Symptoms reported: darkening; no associated systemic symptoms reported; the patient notes the condition has been present for three to twelve months; texture is reported as flat; an image taken at a distance; the lesion involves the back of the hand:
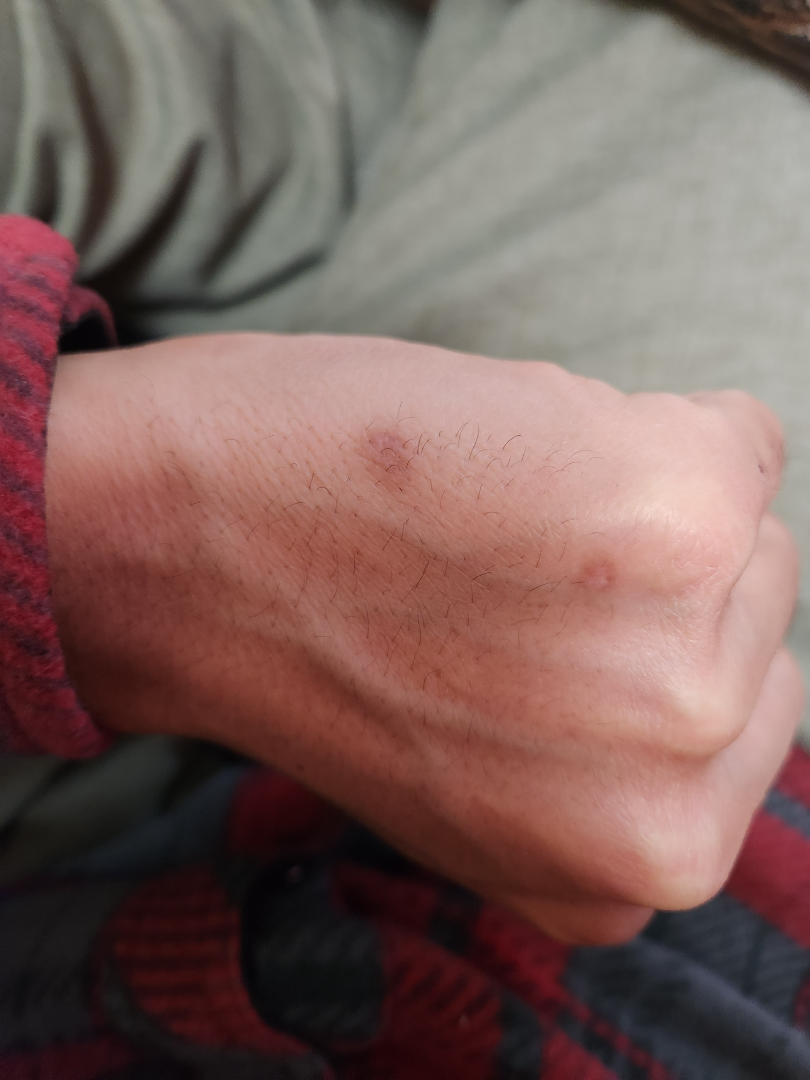On remote review of the image, Prurigo nodularis (leading); Lichen planus/lichenoid eruption (considered); Post-Inflammatory hyperpigmentation (considered); Eczema (lower probability).